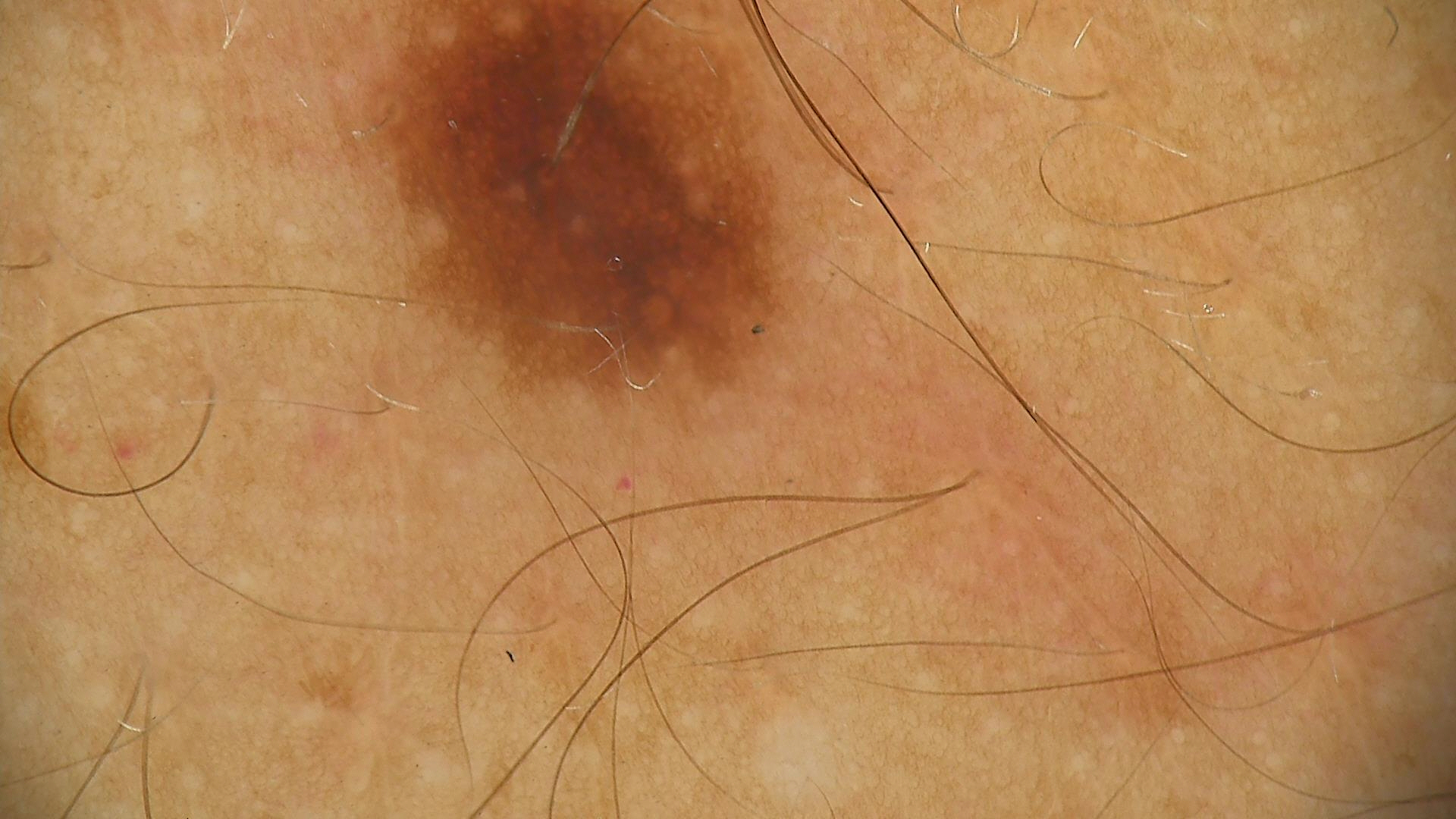Labeled as a dysplastic junctional nevus.